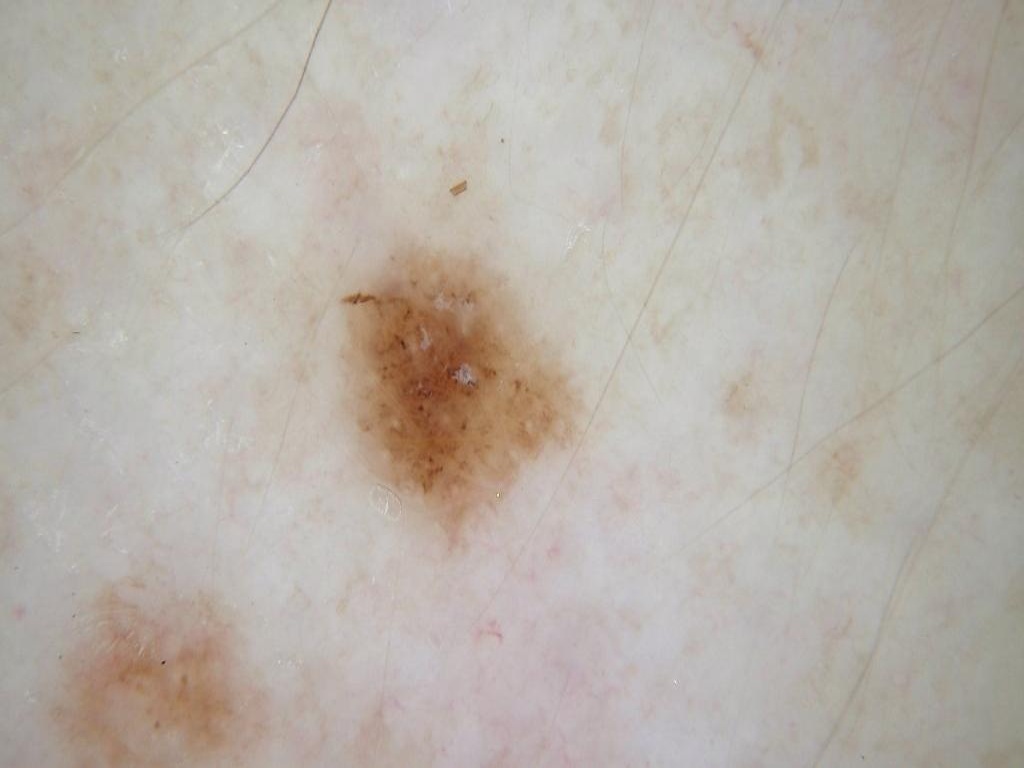A female patient roughly 45 years of age. A dermoscopy image of a single skin lesion. Dermoscopy demonstrates no streaks, globules, milia-like cysts, pigment network, or negative network. The visible lesion spans left=334, top=236, right=580, bottom=548. Consistent with a melanocytic nevus.